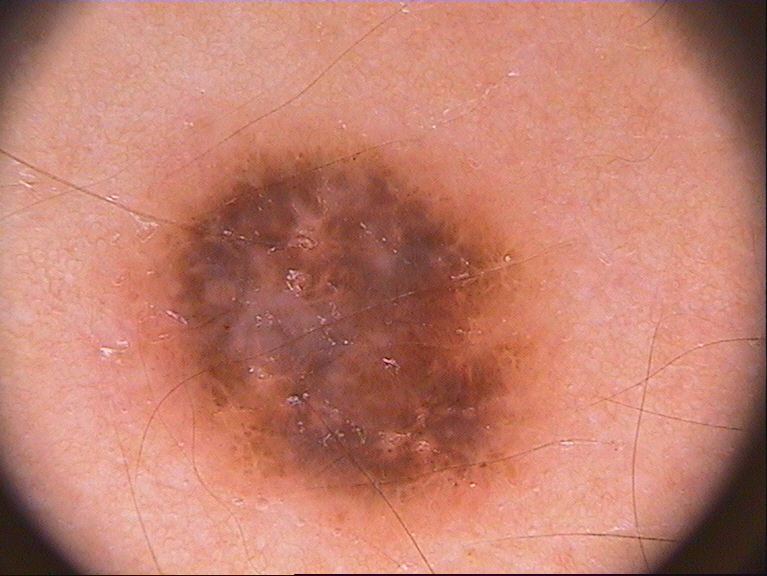Q: What kind of image is this?
A: dermoscopy of a skin lesion
Q: What is the lesion's bounding box?
A: 122 134 550 533
Q: What is this lesion?
A: a melanocytic nevus, a benign skin lesion